The patient says their skin tans without first burning. A female patient age 60. The patient describes having few moles overall. Referred for assessment of suspected basal cell carcinoma — 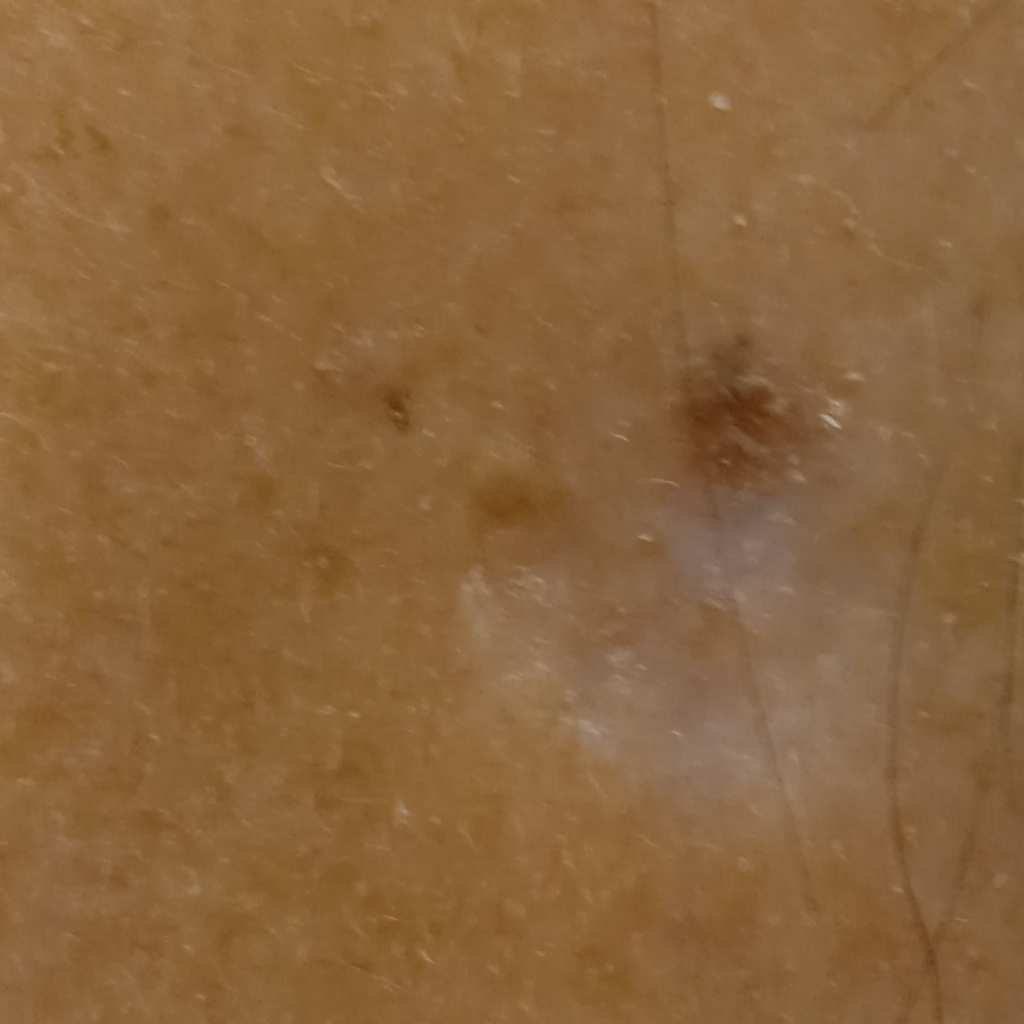The lesion involves the face. The lesion measures approximately 6.6 mm. The biopsy diagnosis was a basal cell carcinoma, following excision, with a measured thickness of 1 mm.